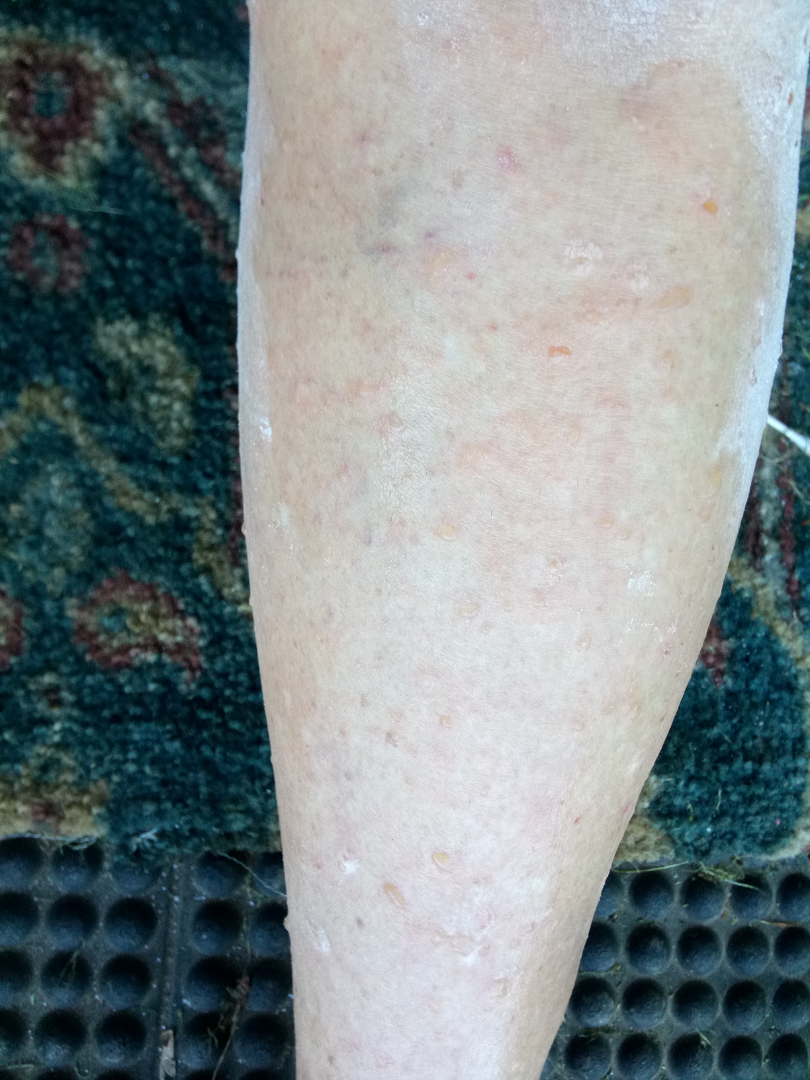The reviewing dermatologist's impression was: Stasis Dermatitis (most likely).